Dermoscopy of a skin lesion: 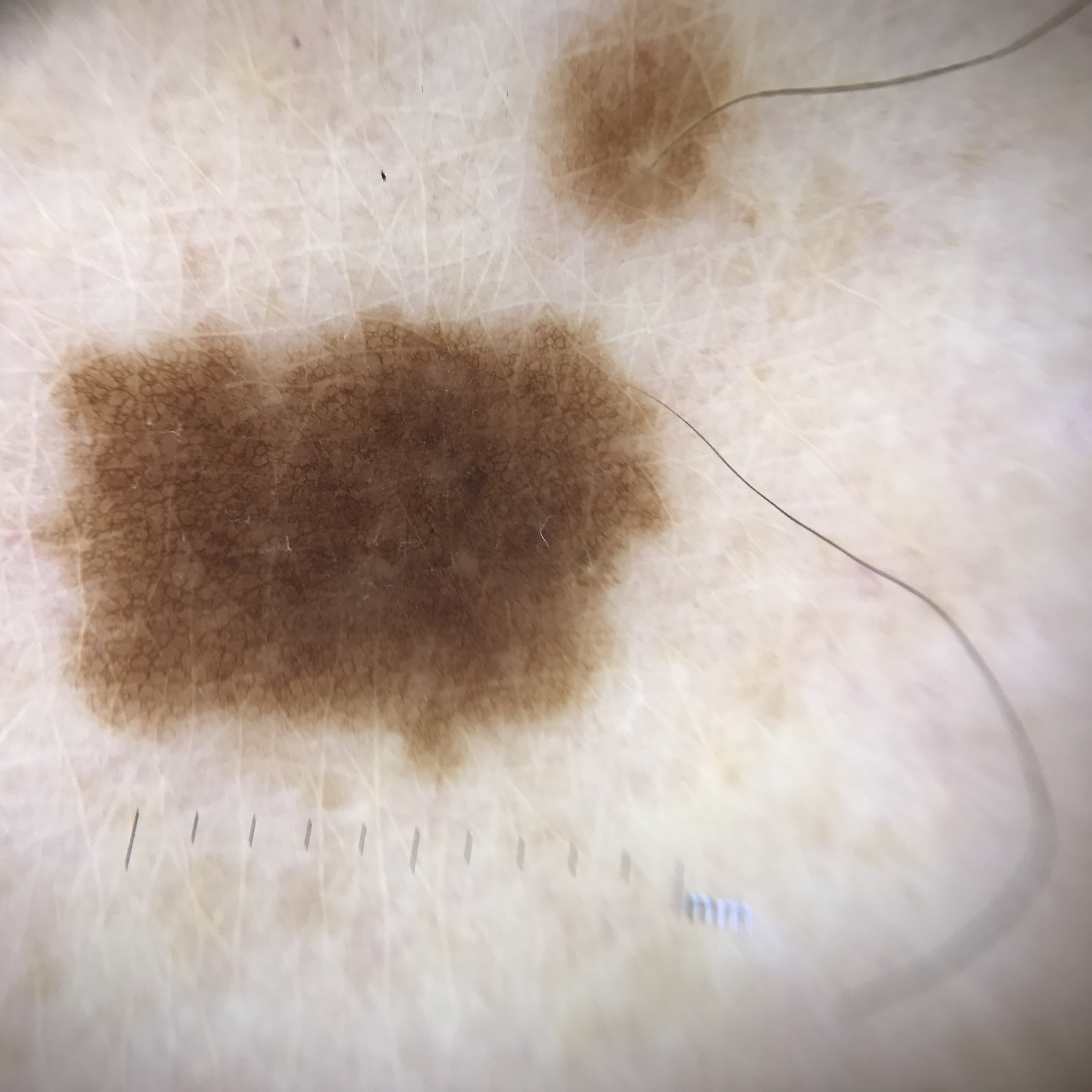The diagnosis was a dysplastic junctional nevus.